The photo was captured at a distance. The leg, head or neck, arm, back of the hand, palm and front of the torso are involved: 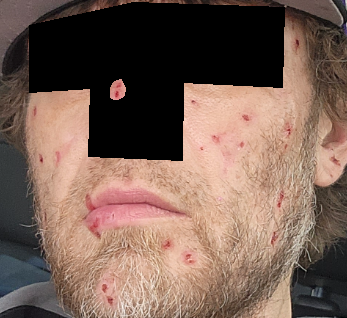One reviewing dermatologist: favoring Inflicted skin lesions; also on the differential is Acne; less probable is Bacterial pyoderma.